The patient is male; a close-up photograph; the arm is involved.
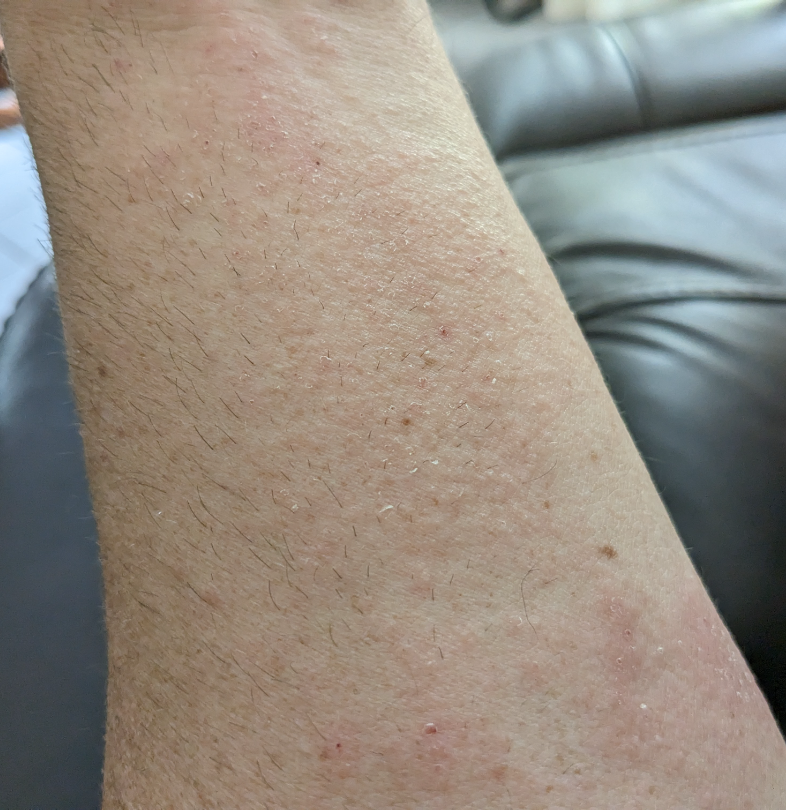Case summary:
• differential: the leading impression is Eczema; an alternative is Irritant Contact Dermatitis; a more distant consideration is Allergic Contact Dermatitis